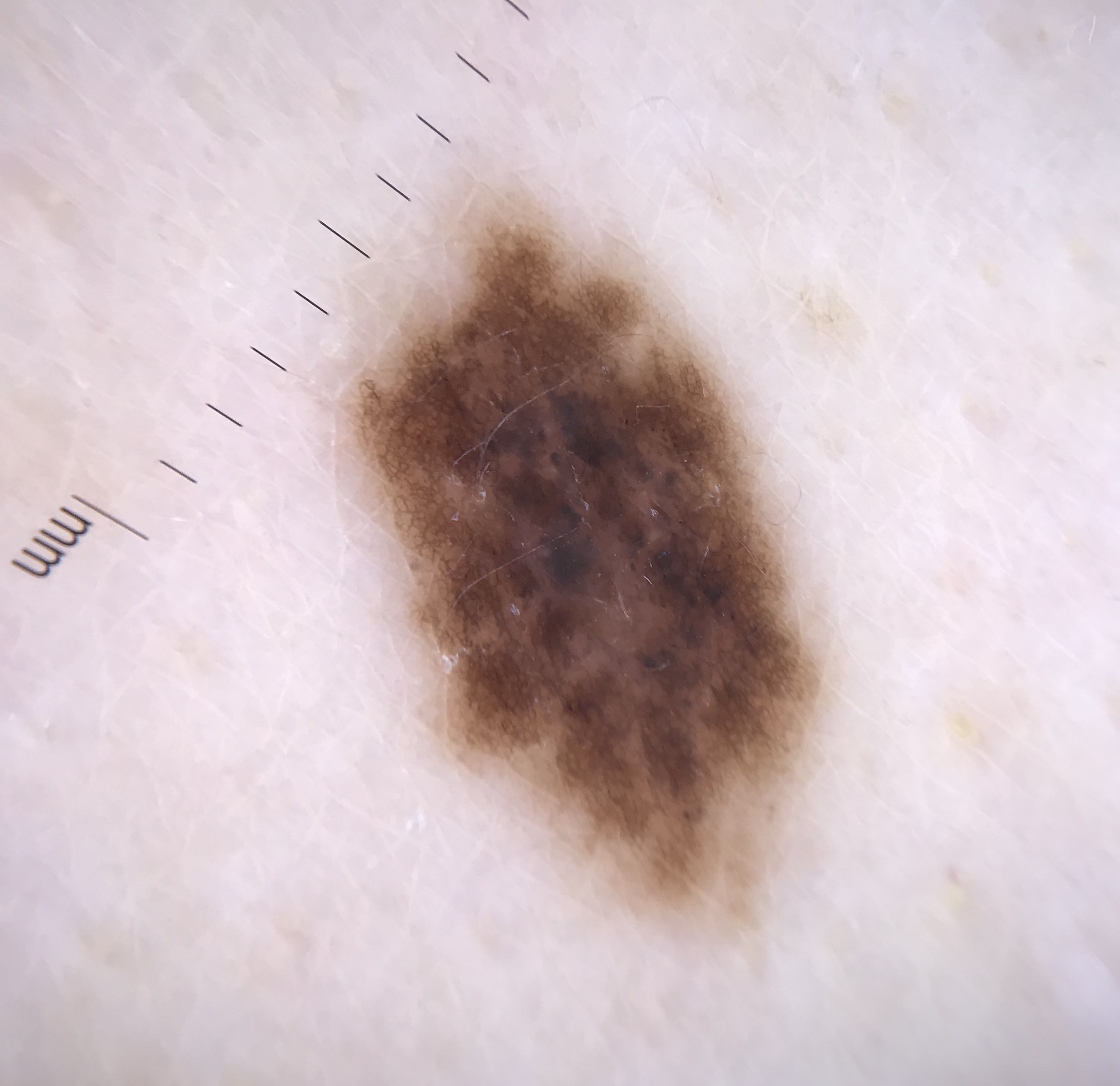Dermoscopy of a skin lesion.
Classified as a banal lesion — a congenital compound nevus.